Located on the leg. The patient also reports joint pain. A close-up photograph. Symptoms reported: bothersome appearance. The contributor notes the lesion is flat. Fitzpatrick phototype IV:
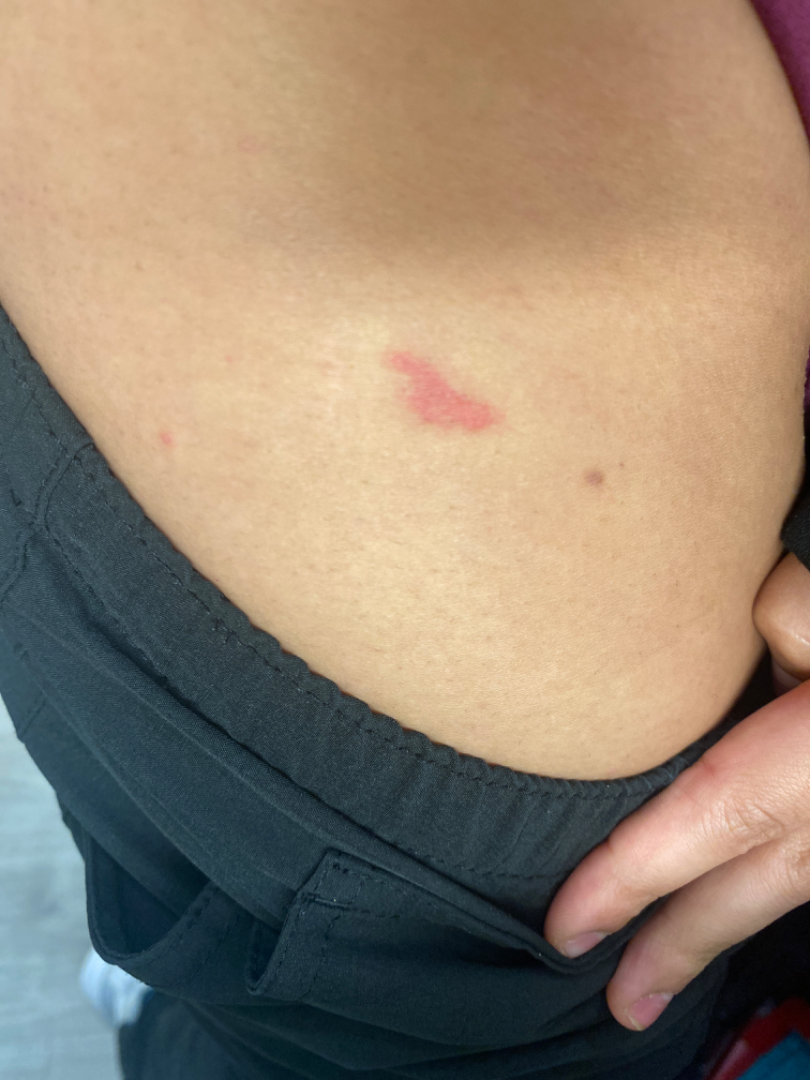The case was difficult to assess from the available photograph.